Texture is reported as raised or bumpy, the patient considered this a rash, present for about one day, no constitutional symptoms were reported, reported lesion symptoms include bothersome appearance and itching, this is a close-up image, the affected area is the arm.
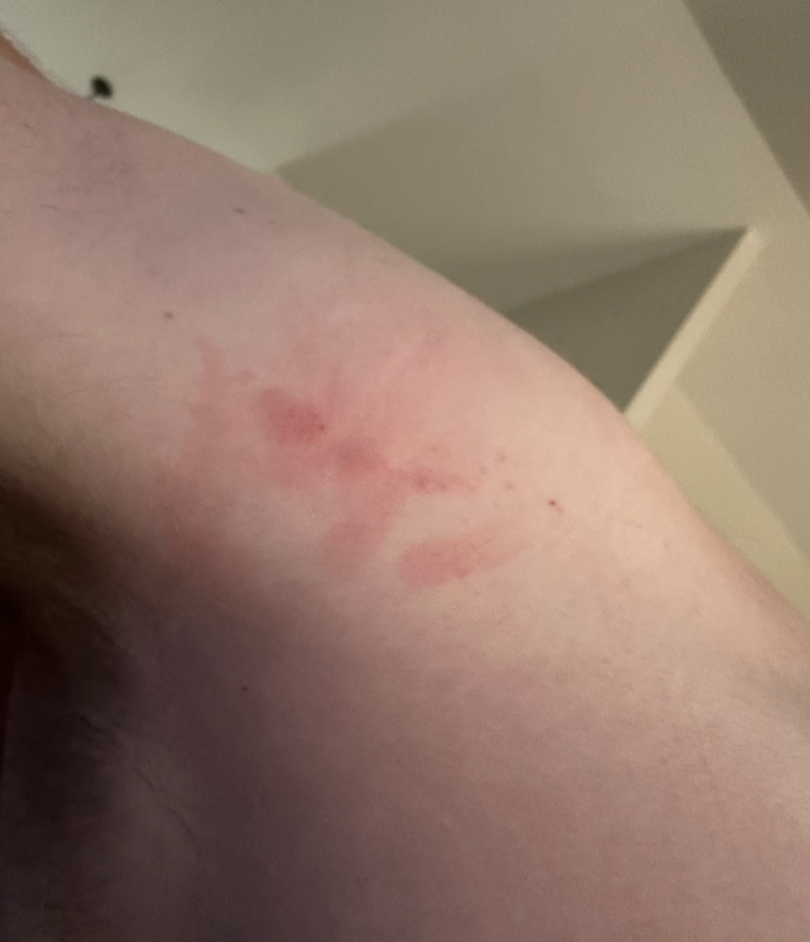The case was difficult to assess from the available photograph.